Female contributor, age 40–49 · this image was taken at an angle · located on the arm.
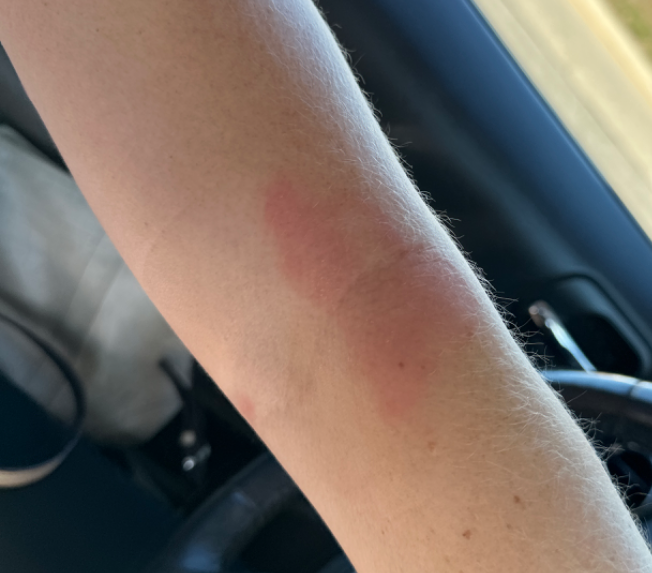present for = more than one year | associated systemic symptoms = joint pain | surface texture = flat and raised or bumpy | differential = favoring Eczema; also consider Allergic Contact Dermatitis; possibly Irritant Contact Dermatitis.